Located on the head or neck; the subject is 50–59, female; an image taken at an angle:
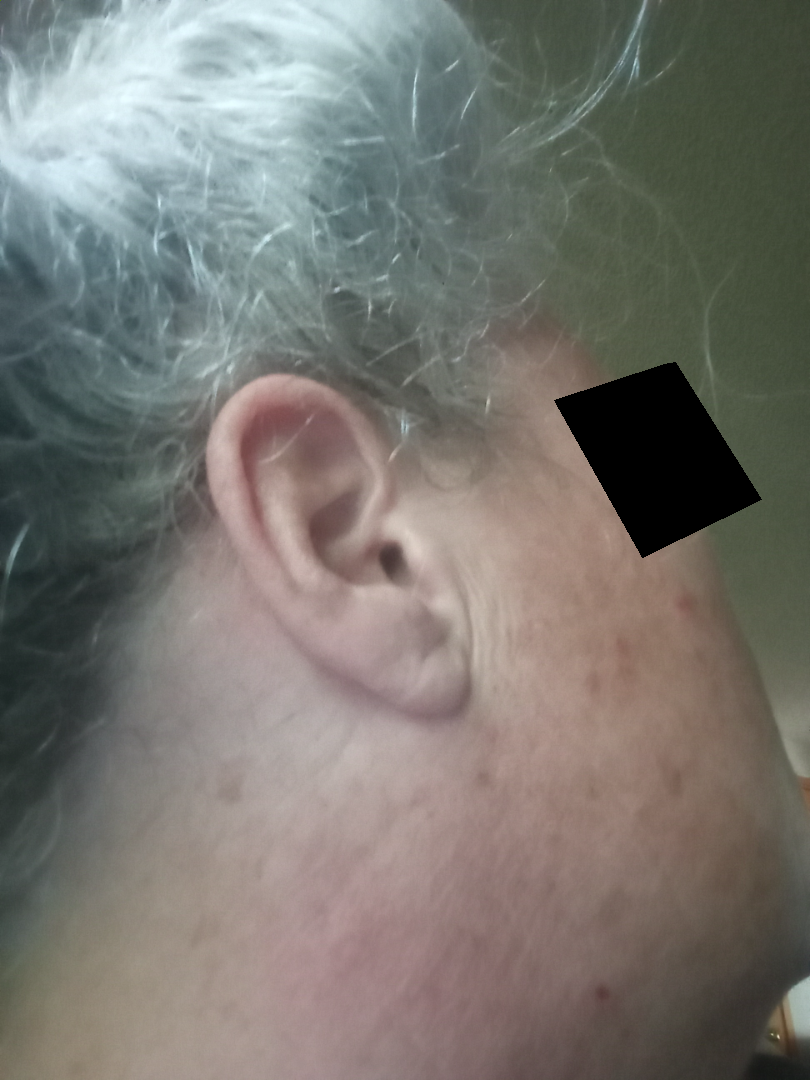The patient reports the condition has been present for less than one week. Symptoms reported: itching, enlargement, bothersome appearance and pain. Most consistent with Acne.